No relevant systemic symptoms · the leg is involved · this image was taken at an angle · self-categorized by the patient as a rash · reported duration is less than one week · texture is reported as raised or bumpy:
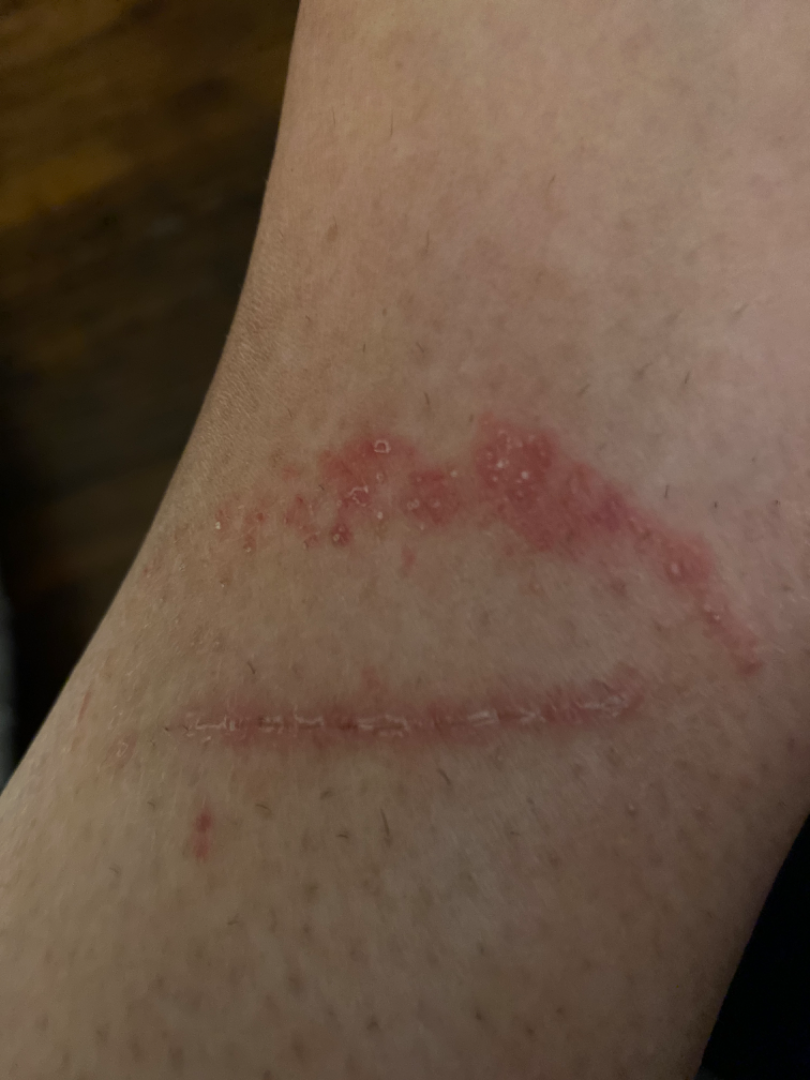A single dermatologist reviewed the case: the impression is Allergic Contact Dermatitis.